A dermoscopic view of a skin lesion, the subject is a female aged 23 to 27:
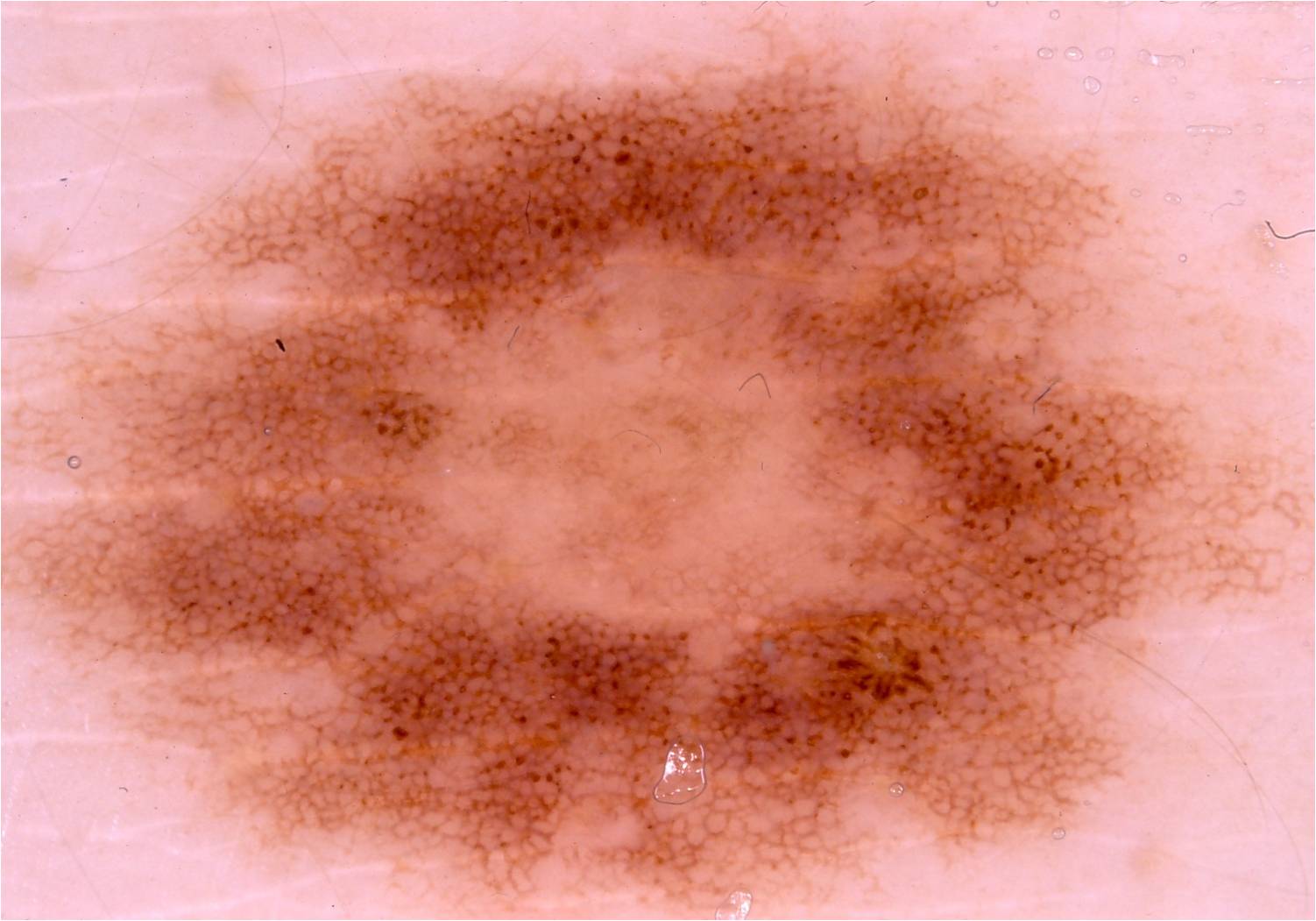Dermoscopic assessment notes globules and pigment network; no streaks, negative network, or milia-like cysts. The lesion reaches across nearly the entire image. The clinical diagnosis was a melanocytic nevus.